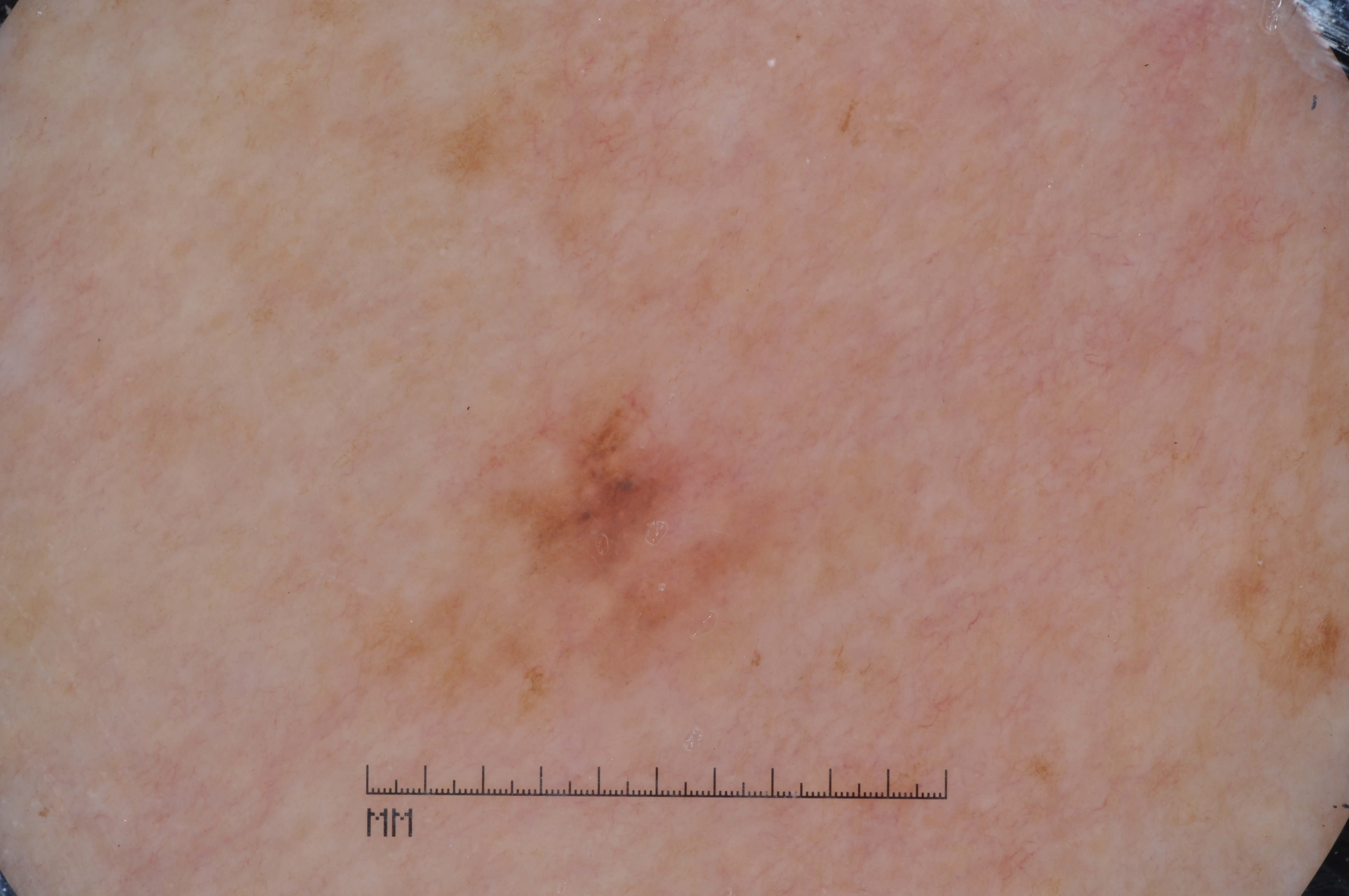subject = female, approximately 60 years of age
image type = dermoscopy
extent = small
dermoscopic pattern = pigment network and milia-like cysts; absent: negative network and streaks
bounding box = (369, 385, 790, 707)
diagnostic label = a melanoma, a malignancy